Referred for assessment of suspected basal cell carcinoma; dermoscopy of a skin lesion; a female patient 60 years old.
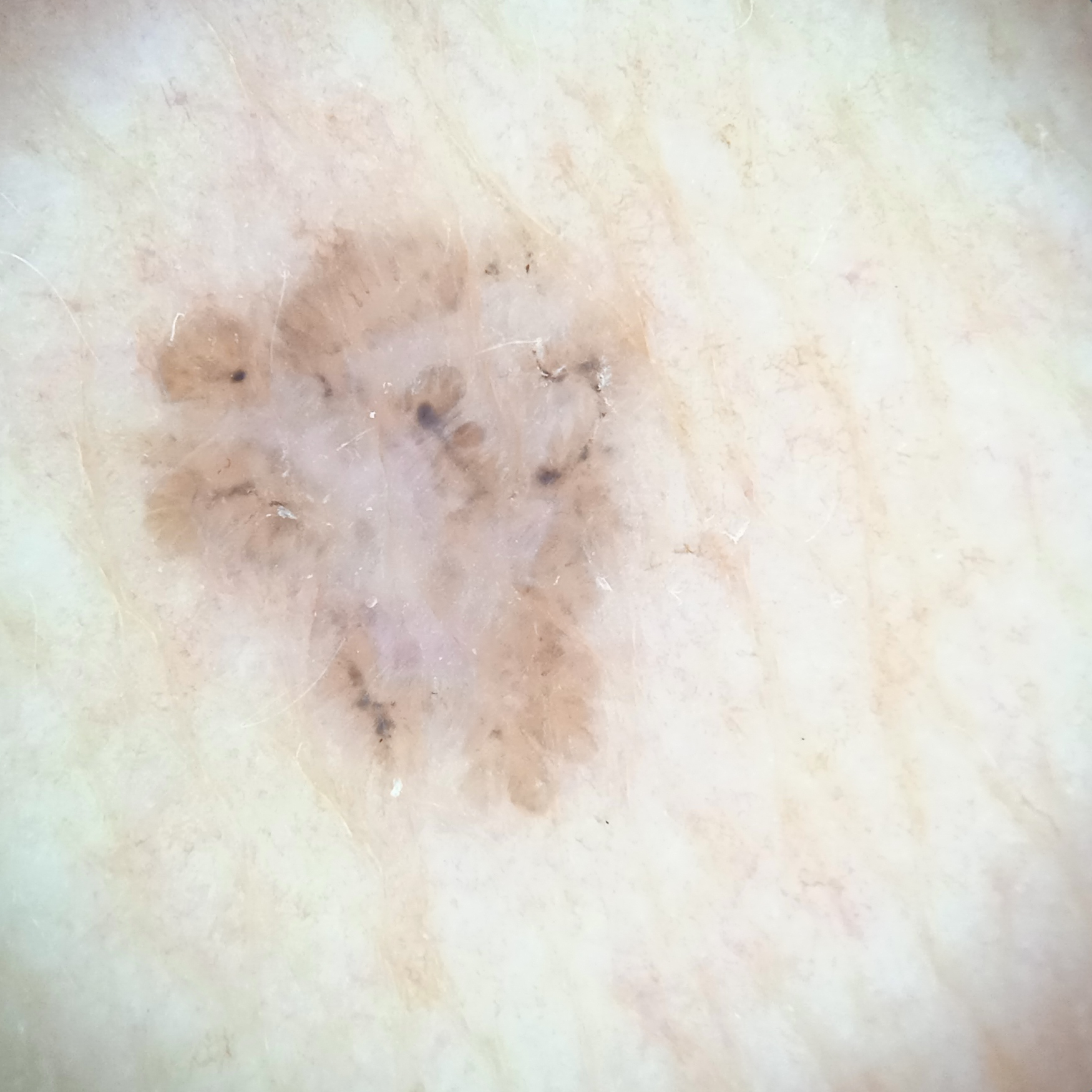The lesion involves the torso.
Measuring roughly 7.2 mm.
The diagnostic impression was a basal cell carcinoma.